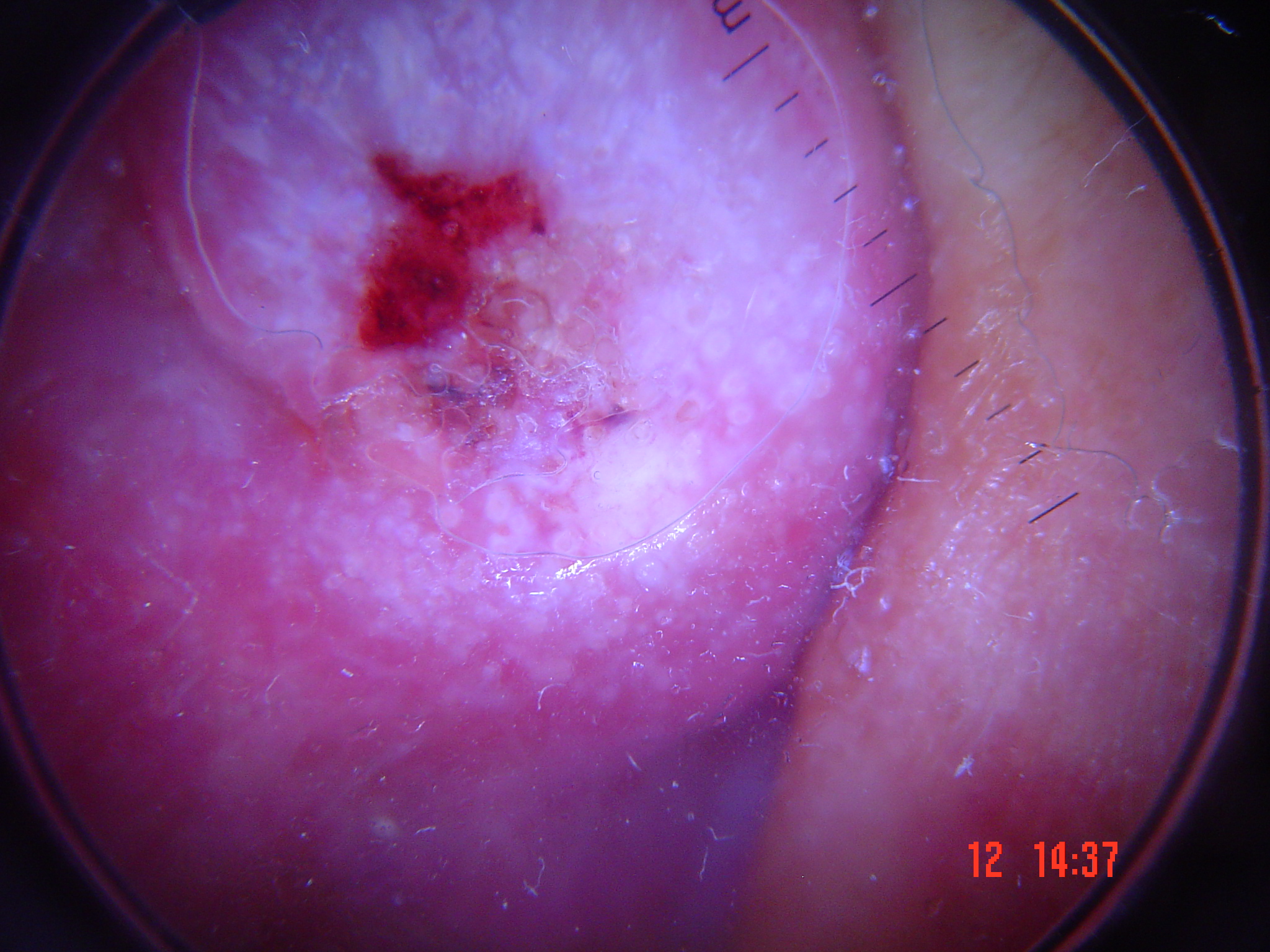class = squamous cell carcinoma (biopsy-proven)